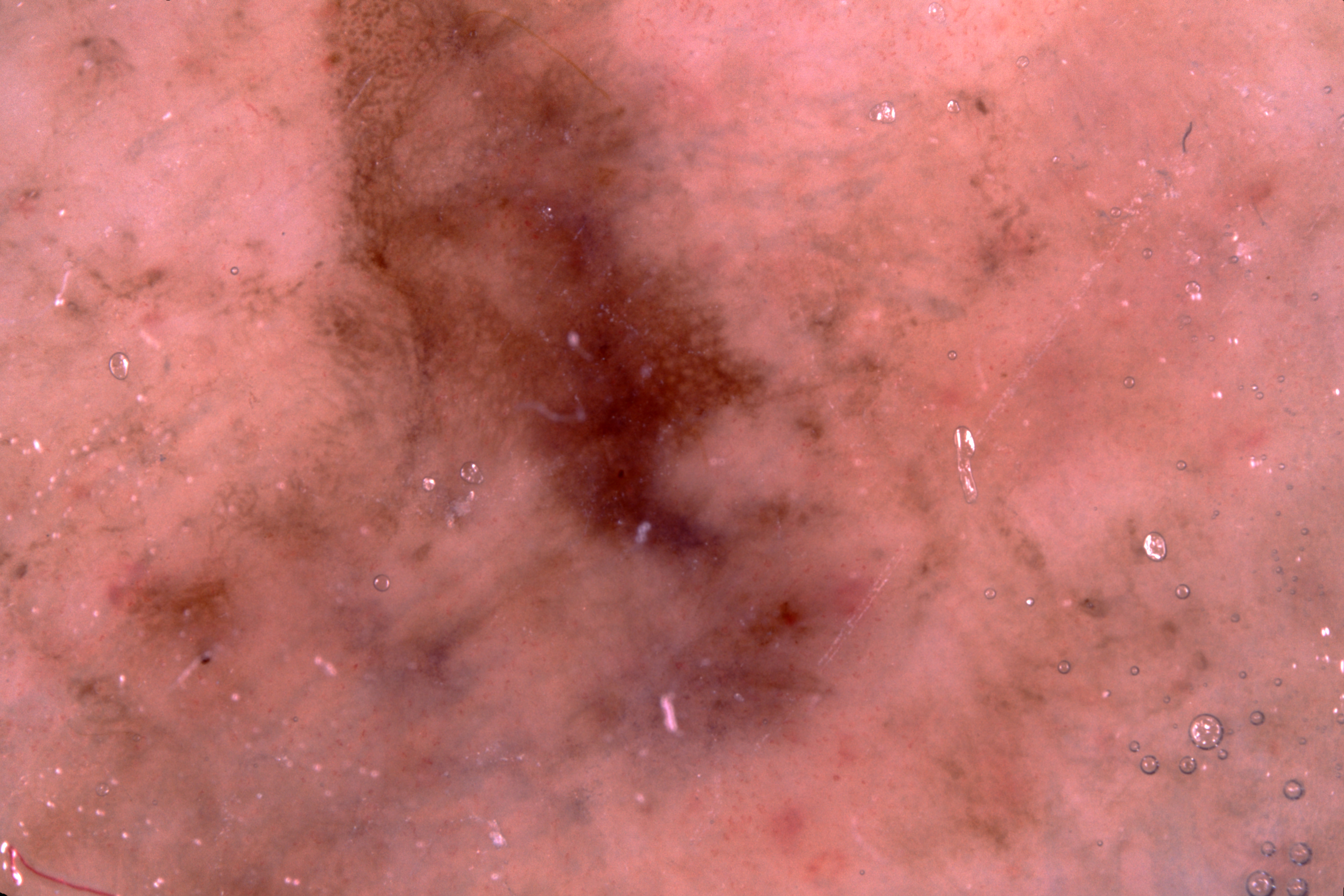Q: What kind of image is this?
A: dermatoscopic image of a skin lesion
Q: Where is the lesion in the image?
A: extends across the entire field of view
Q: What is this lesion?
A: a melanoma, a malignant skin lesion